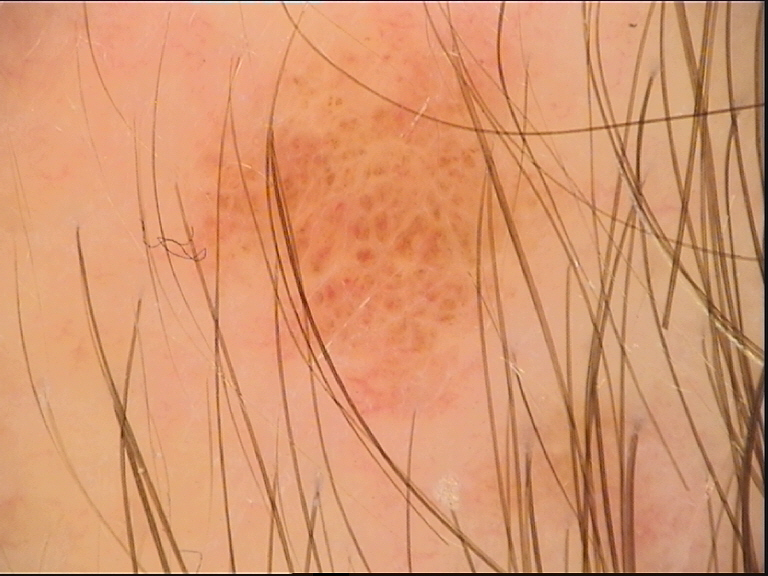  diagnosis:
    name: compound nevus
    code: cb
    malignancy: benign
    super_class: melanocytic
    confirmation: expert consensus